A dermoscopic close-up of a skin lesion.
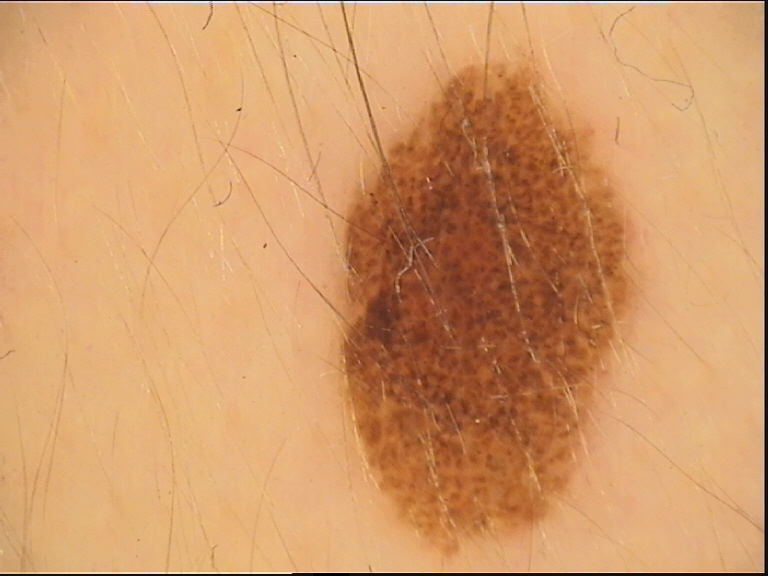* class: dysplastic compound nevus (expert consensus)